Dermoscopy of a skin lesion.
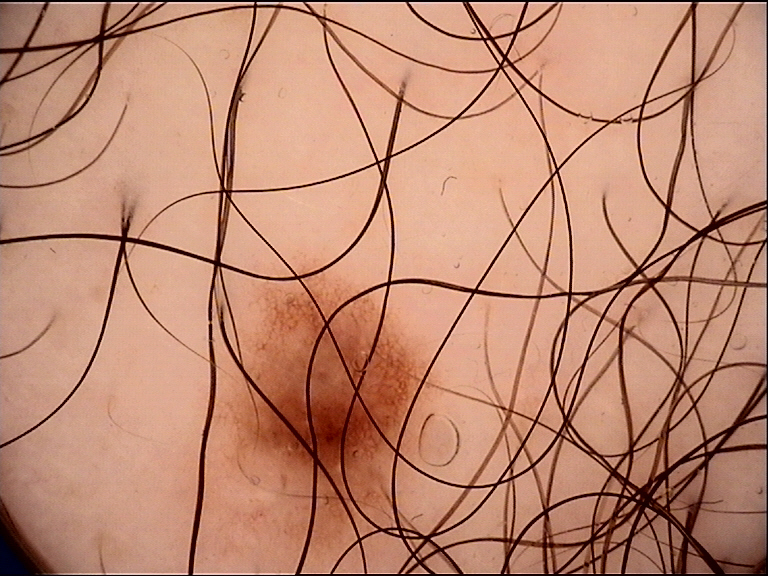Conclusion:
The diagnosis was a dysplastic junctional nevus.